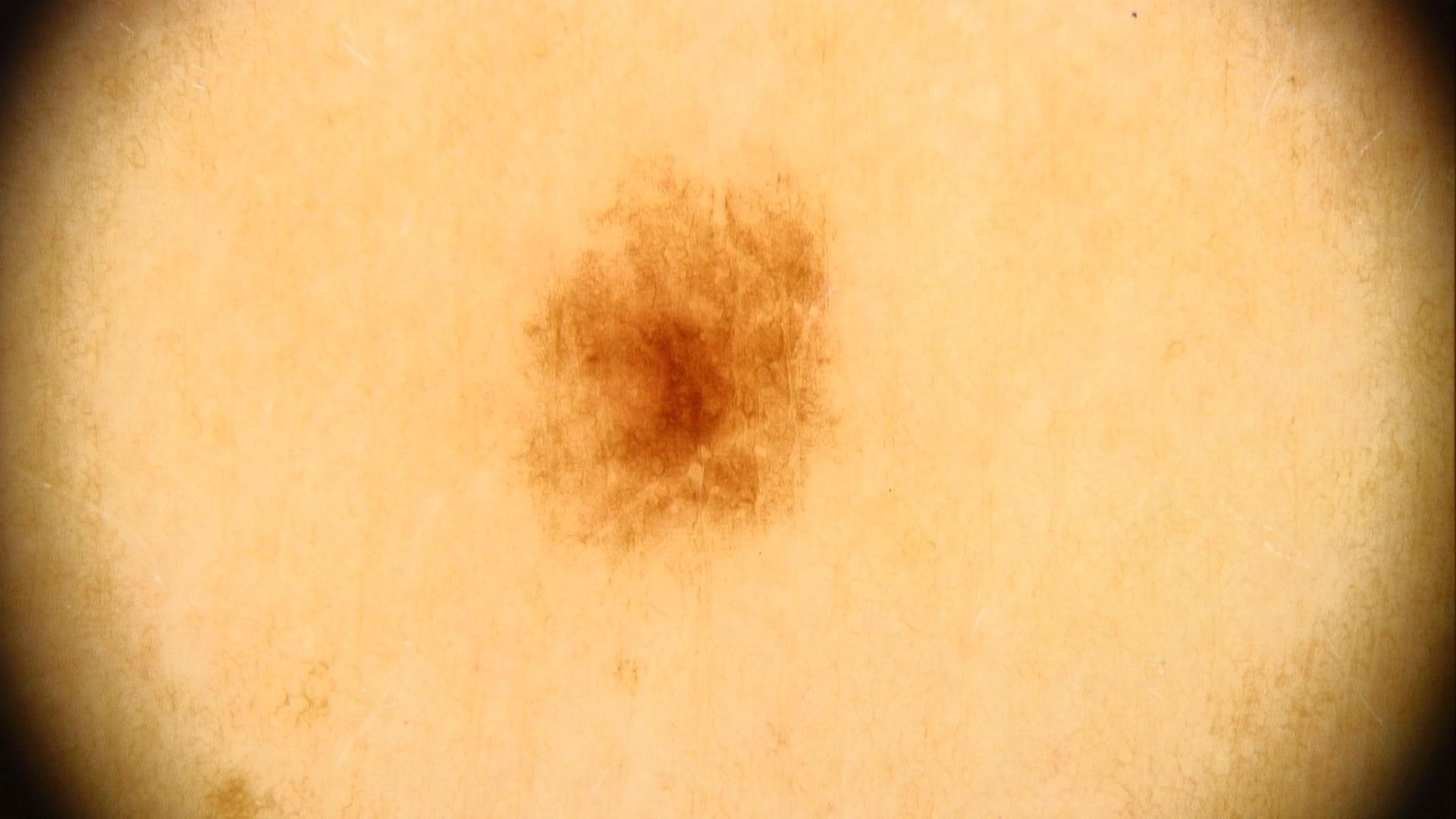patient = male, approximately 40 years of age
imaging = contact-polarized dermoscopy
FST = III
melanoma history = a first-degree relative with melanoma but no prior melanoma
site = the trunk
assessment = Nevus